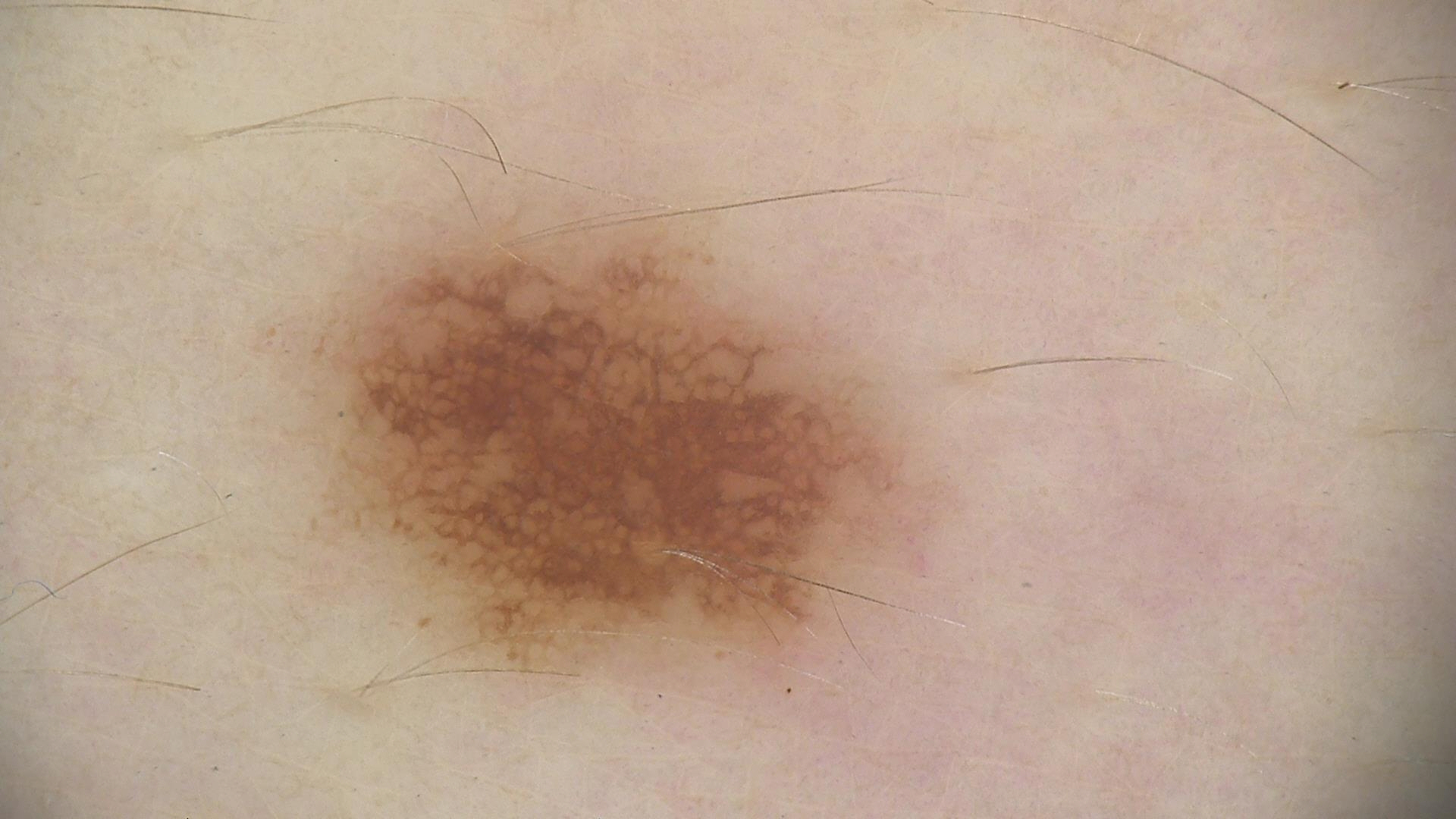Findings: A skin lesion imaged with a dermatoscope. Conclusion: Classified as a benign lesion — a dysplastic junctional nevus.